A dermoscopy image of a single skin lesion.
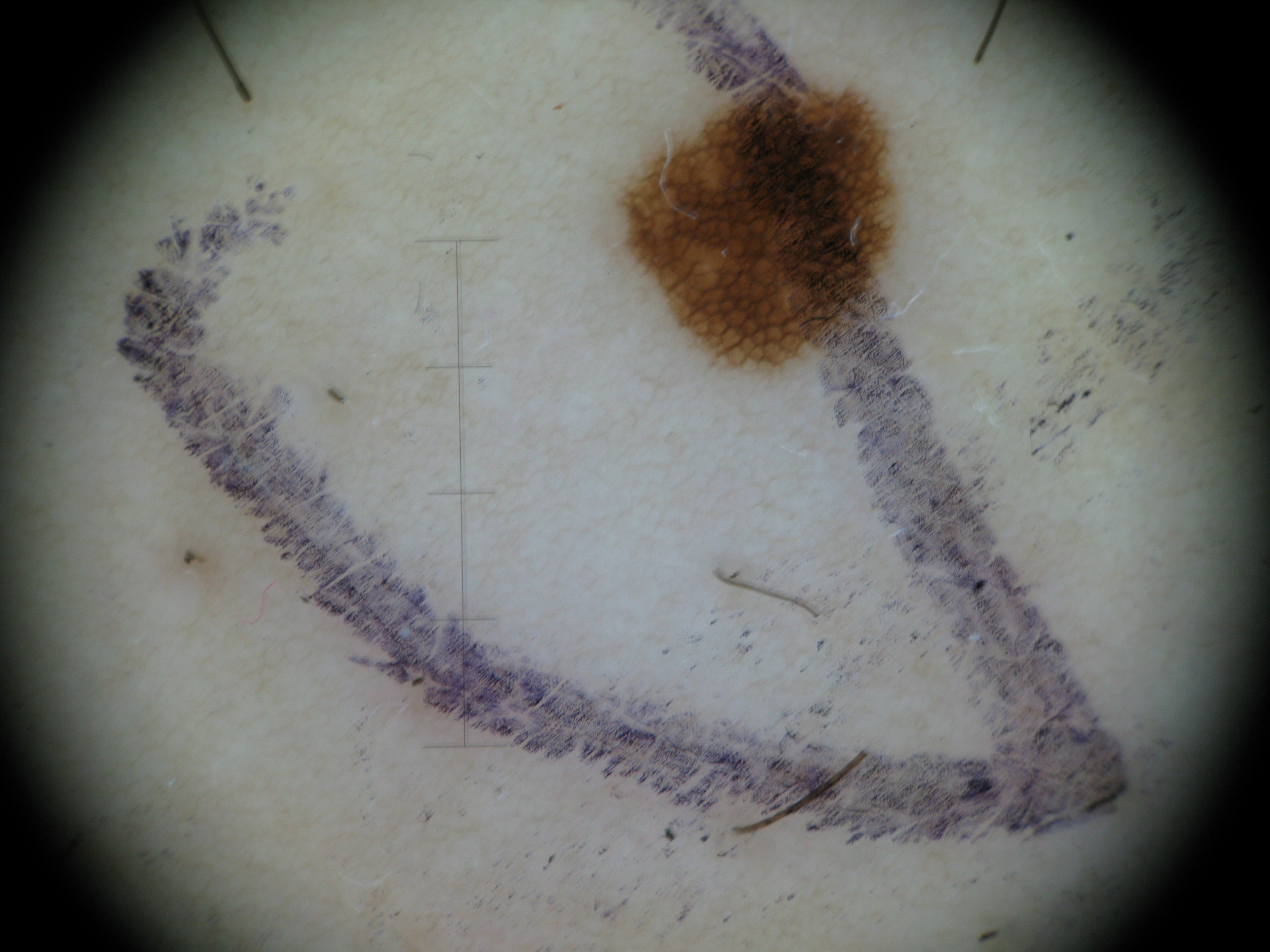{"lesion_type": {"main_class": "banal", "pattern": "junctional"}, "diagnosis": {"name": "junctional nevus", "code": "jb", "malignancy": "benign", "super_class": "melanocytic", "confirmation": "expert consensus"}}